Female contributor, age 40–49; an image taken at a distance; the lesion involves the leg — 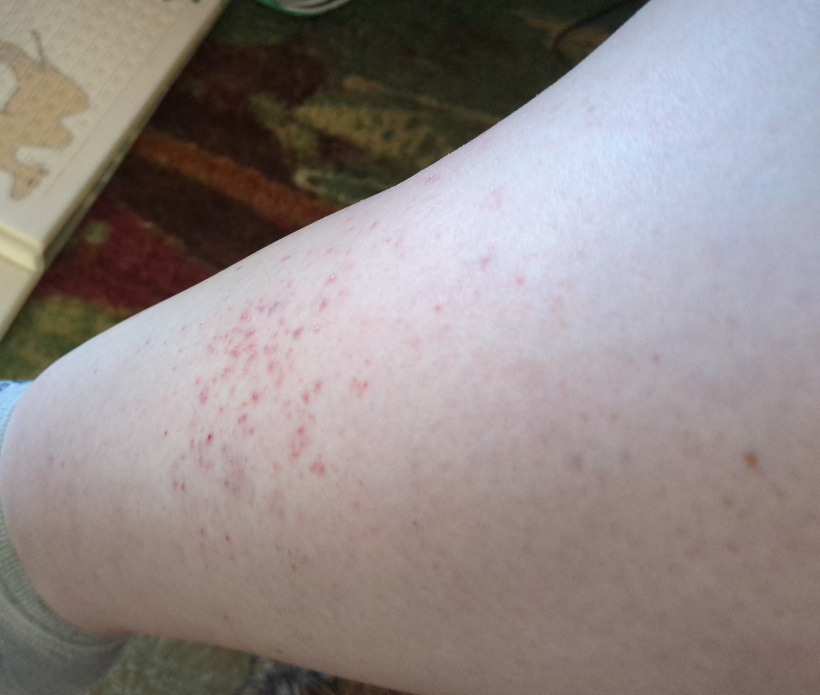| key | value |
|---|---|
| onset | less than one week |
| lesion texture | raised or bumpy |
| patient's own categorization | a rash |
| symptoms | itching, burning, bothersome appearance, enlargement and pain |
| dermatologist impression | favoring Leukocytoclastic Vasculitis; also consider Pigmented purpuric eruption |